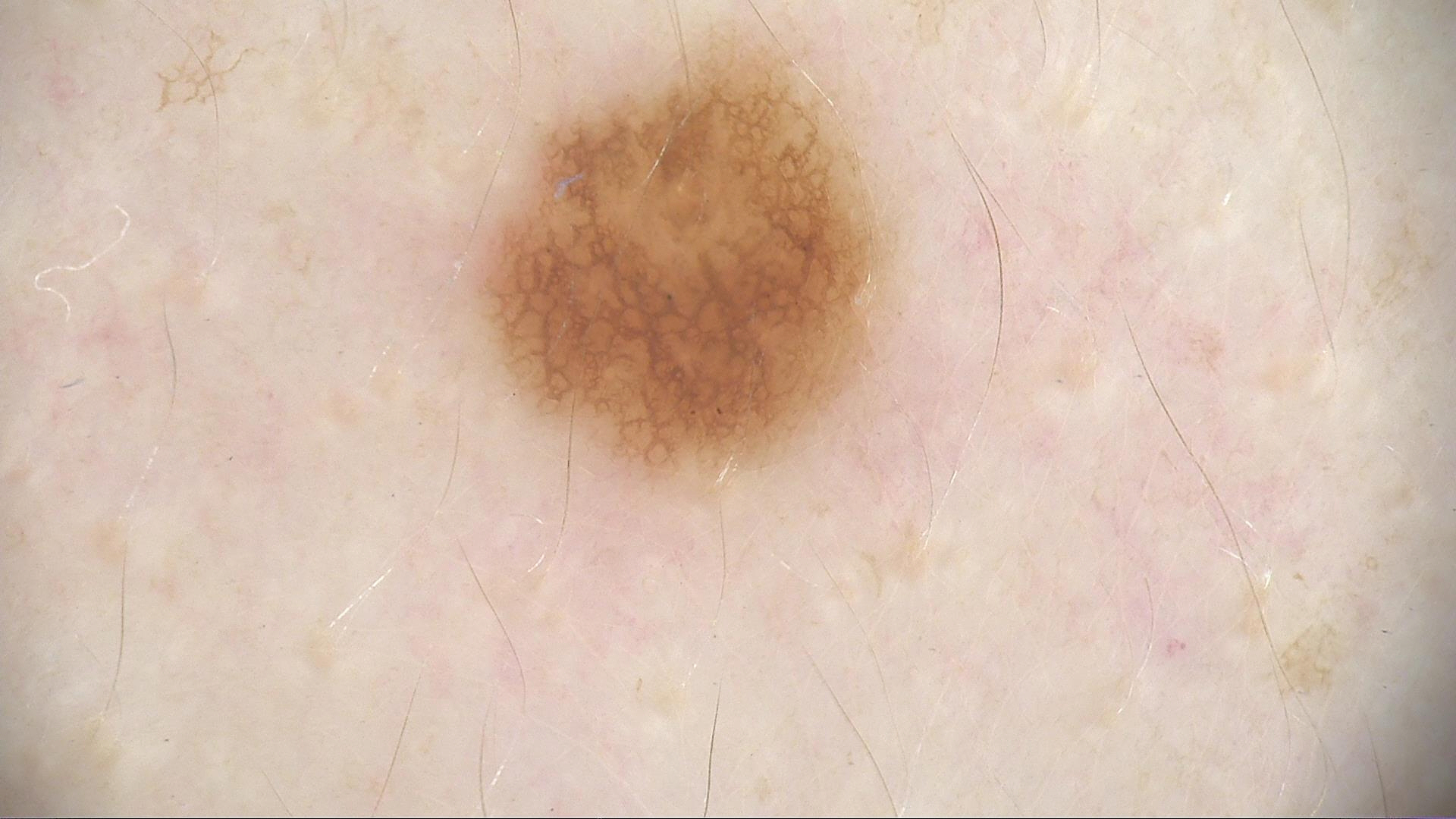A skin lesion imaged with a dermatoscope. Diagnosed as a dysplastic junctional nevus.